A dermoscopic close-up of a skin lesion.
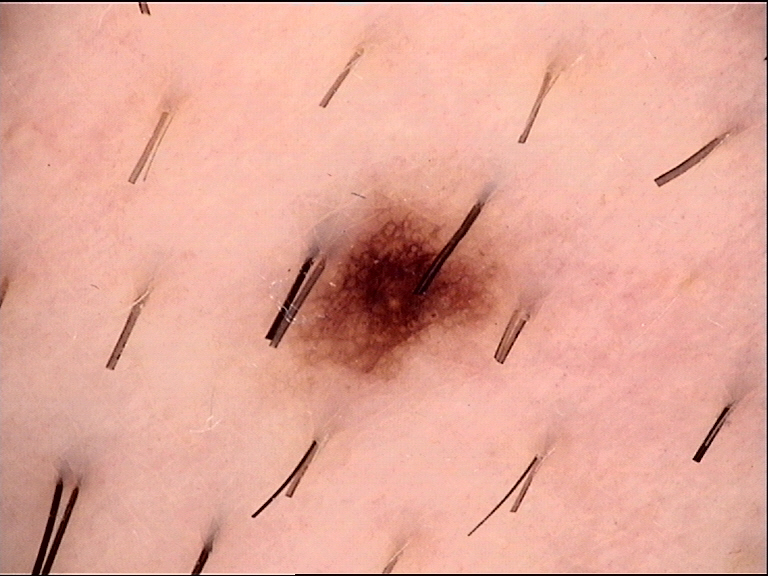class = dysplastic junctional nevus (expert consensus).